Present for three to twelve months. A close-up photograph — 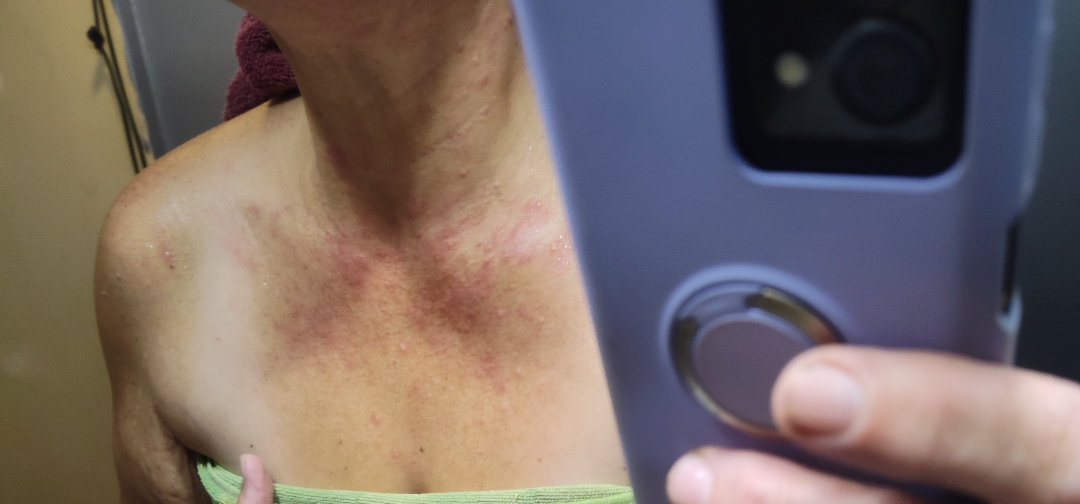clinical impression = Photodermatitis and Allergic Contact Dermatitis were considered with similar weight; less probable is Cutaneous lupus.